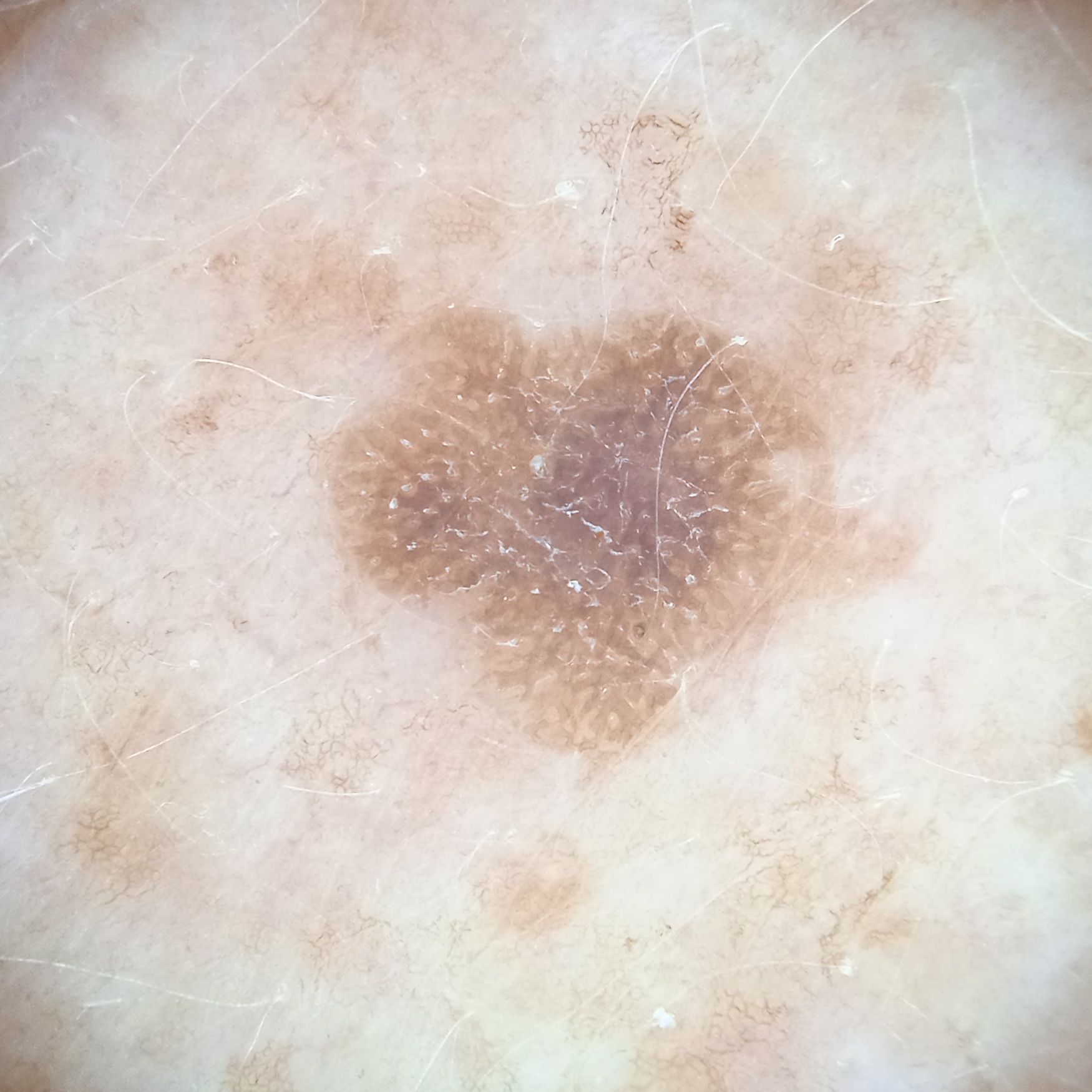Dermoscopy of a skin lesion. A female subject age 78. The lesion is about 5.6 mm across. The dermatologists' assessment was a seborrheic keratosis.